A dermoscopic image of a skin lesion.
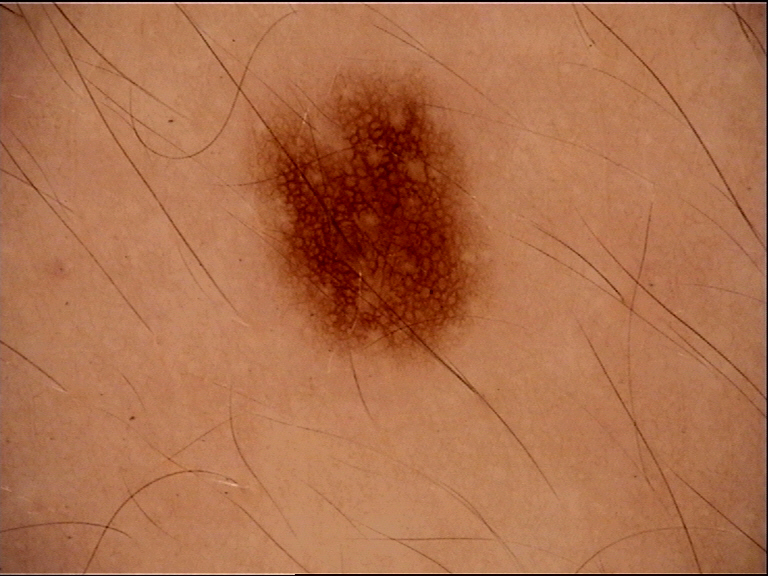This is a banal lesion.
Consistent with a junctional nevus.